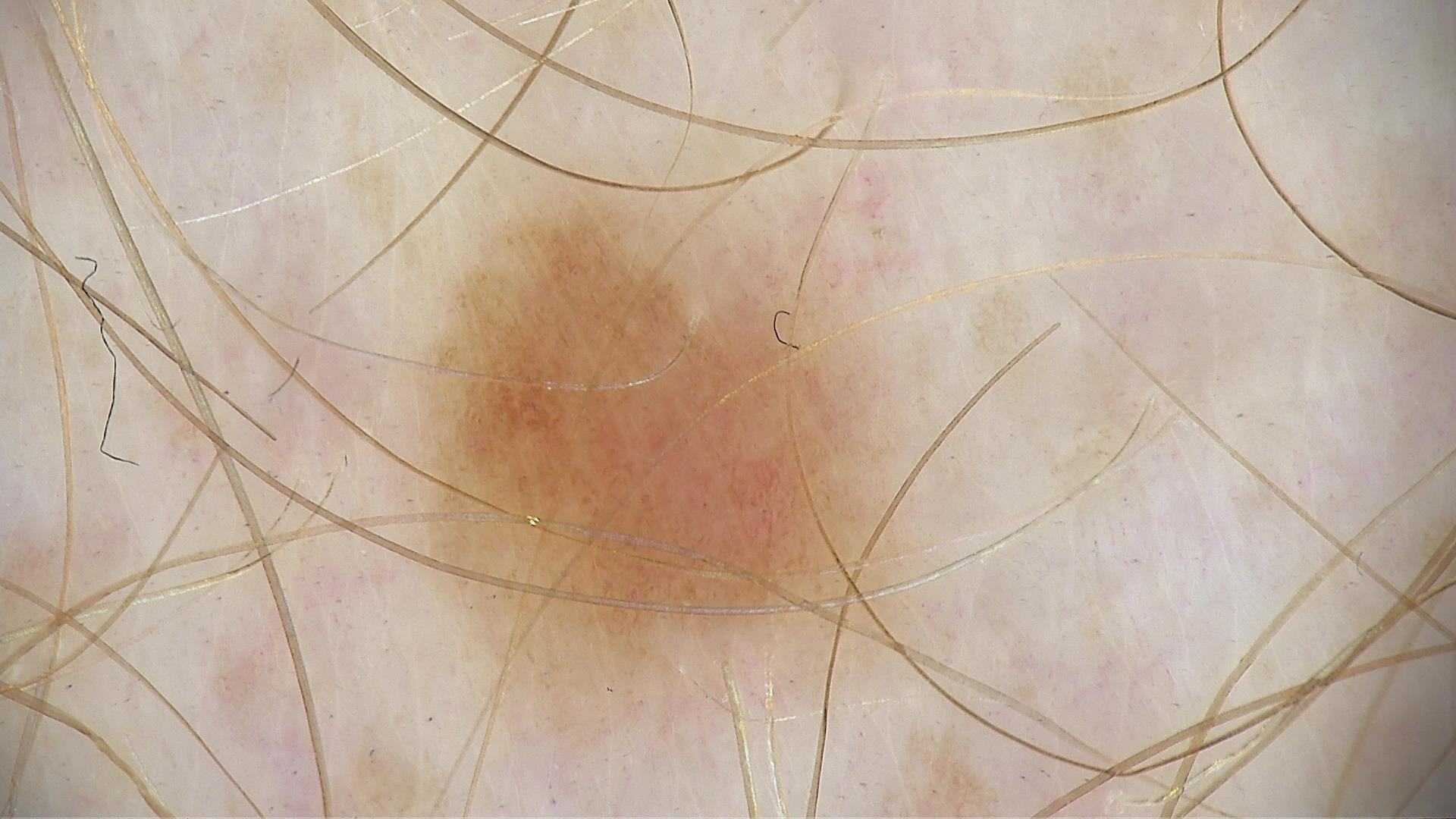Findings:
• assessment: dysplastic junctional nevus (expert consensus)